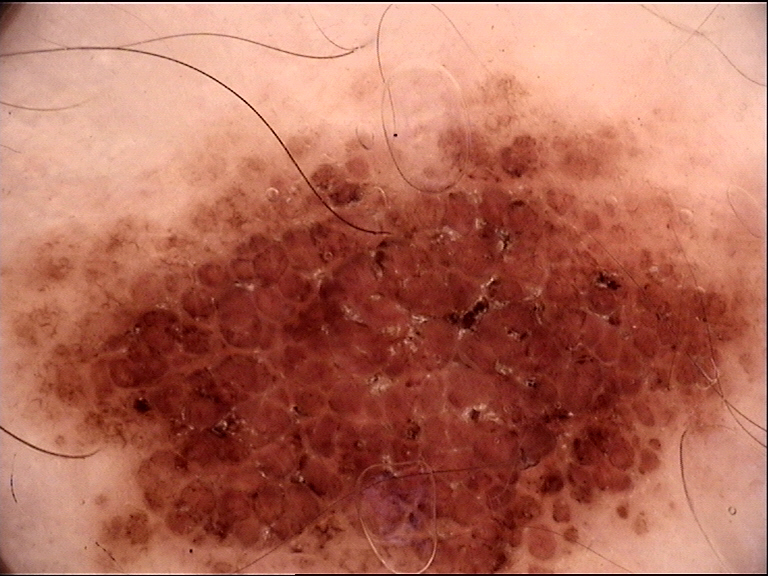– imaging — dermoscopy
– label — dysplastic compound nevus (expert consensus)